A male patient 79 years of age; a clinical photo of a skin lesion taken with a smartphone; the patient was assessed as Fitzpatrick skin type III:
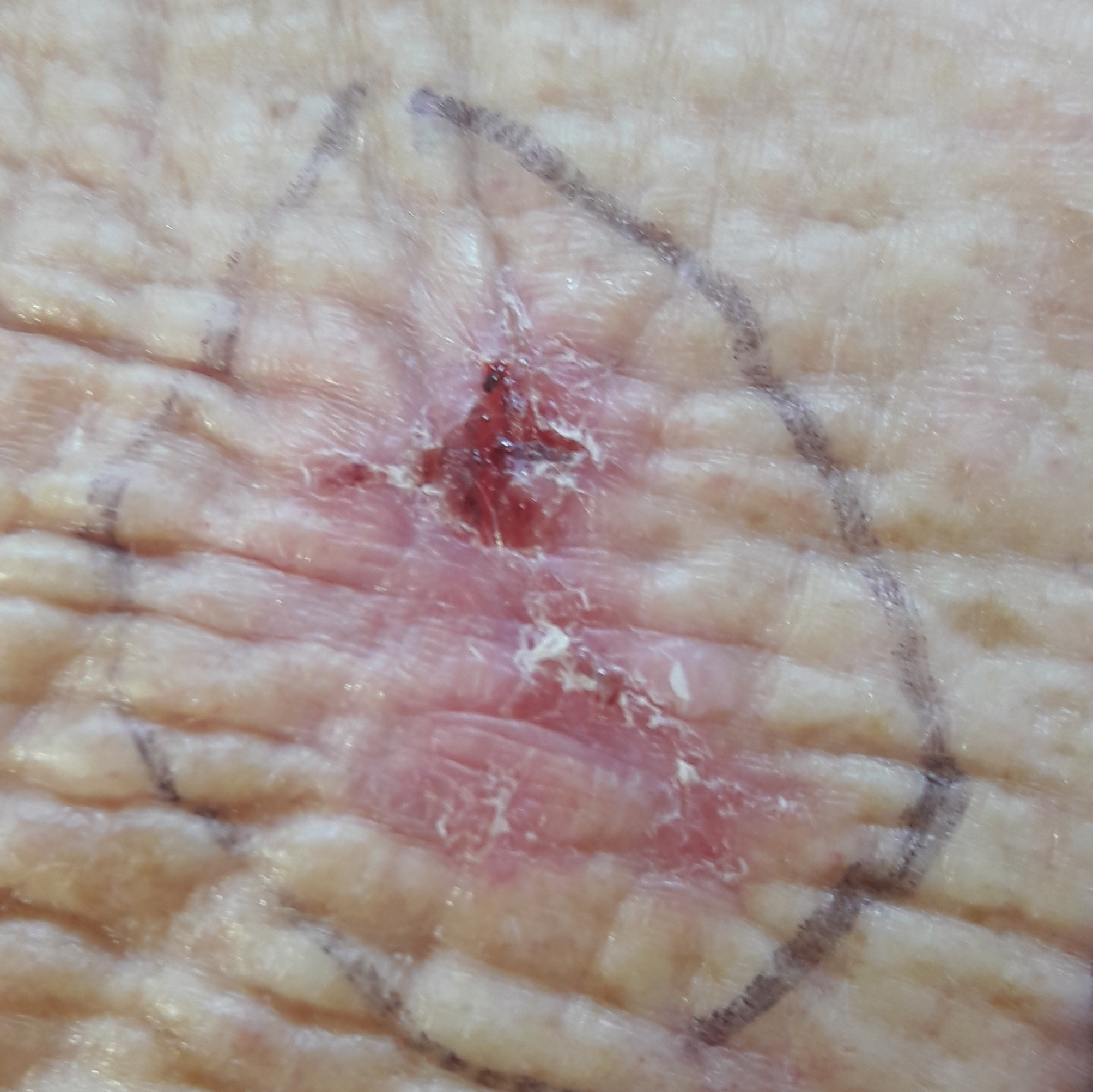diameter=approx. 20 × 10 mm; diagnostic label=squamous cell carcinoma (biopsy-proven).